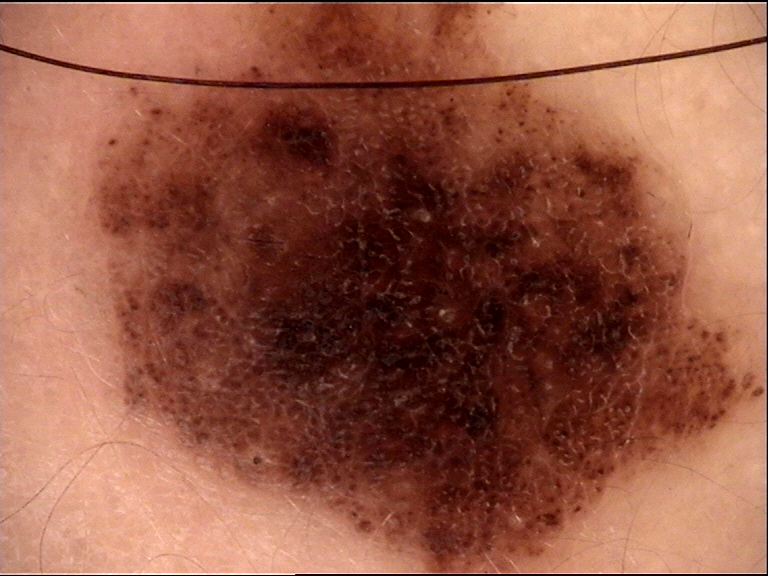label=dysplastic compound nevus (expert consensus).